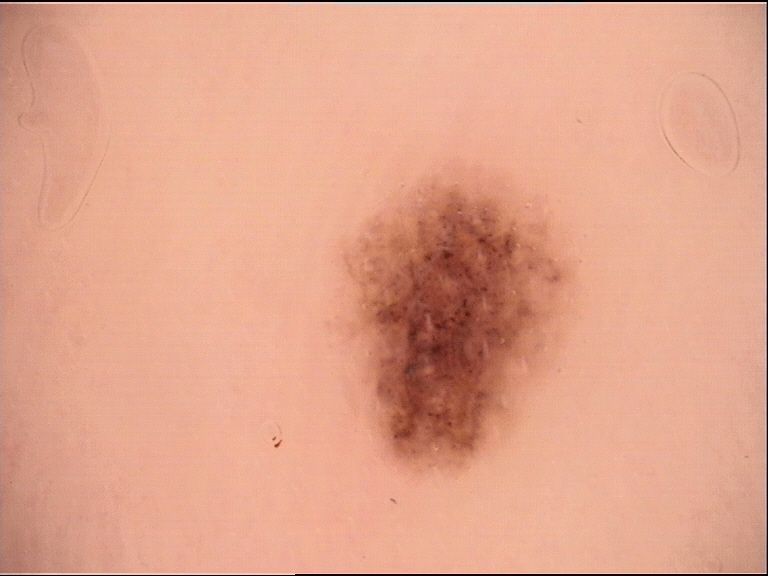Findings:
* modality · dermoscopy
* diagnosis · acral dysplastic junctional nevus (expert consensus)